Dermoscopy of a skin lesion.
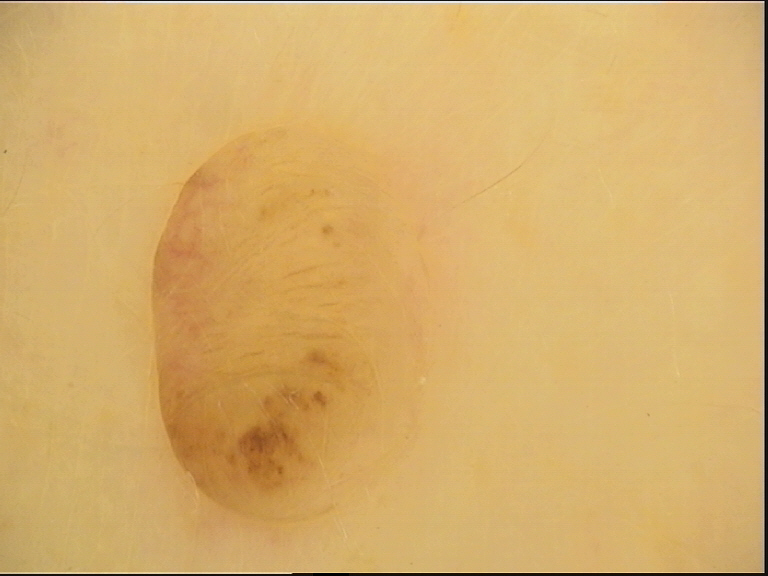Impression: The diagnosis was a banal lesion — a dermal nevus.